A close-up photograph; the affected area is the top or side of the foot; the lesion is described as raised or bumpy; no constitutional symptoms were reported; the patient indicates burning, pain and itching; the patient is 18–29, male.
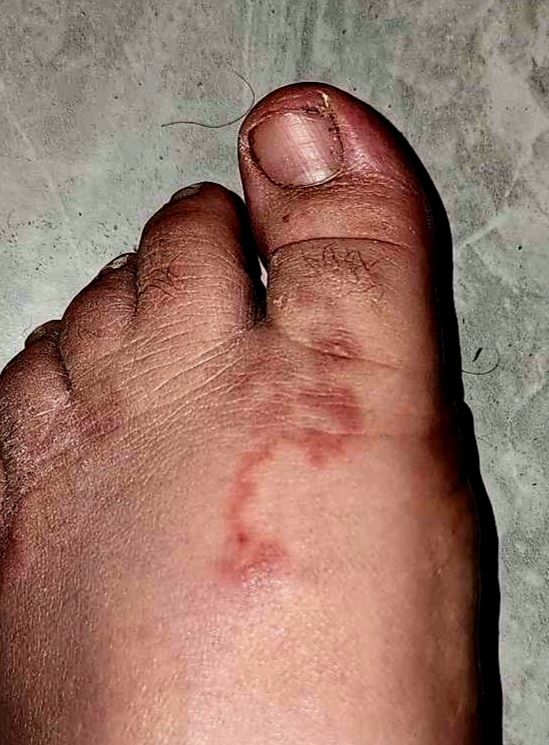Most consistent with Cutaneous larva migrans.